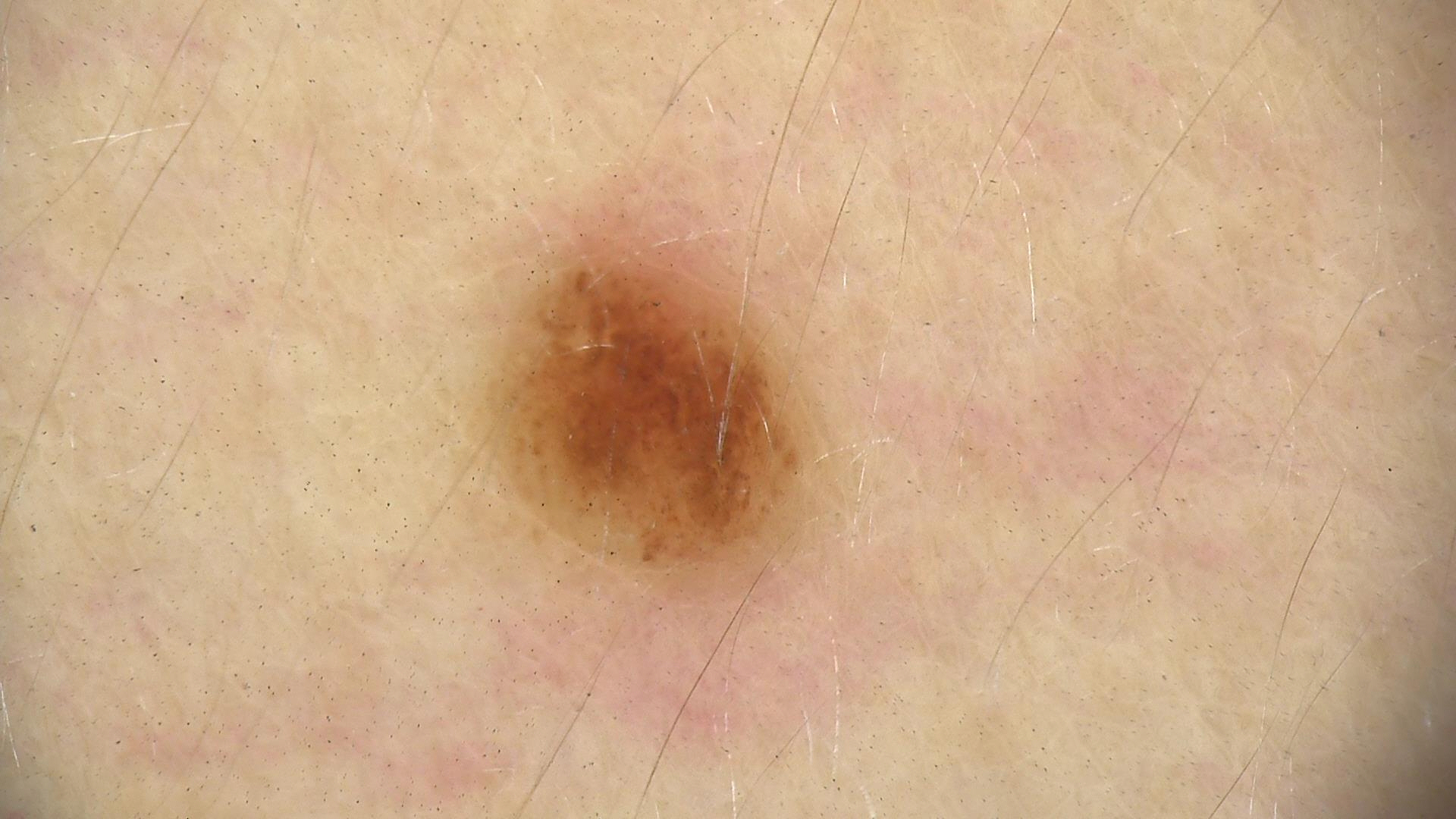image: dermatoscopy
diagnosis:
  name: dysplastic compound nevus
  code: cd
  malignancy: benign
  super_class: melanocytic
  confirmation: expert consensus